The lesion involves the back of the torso. An image taken at an angle:
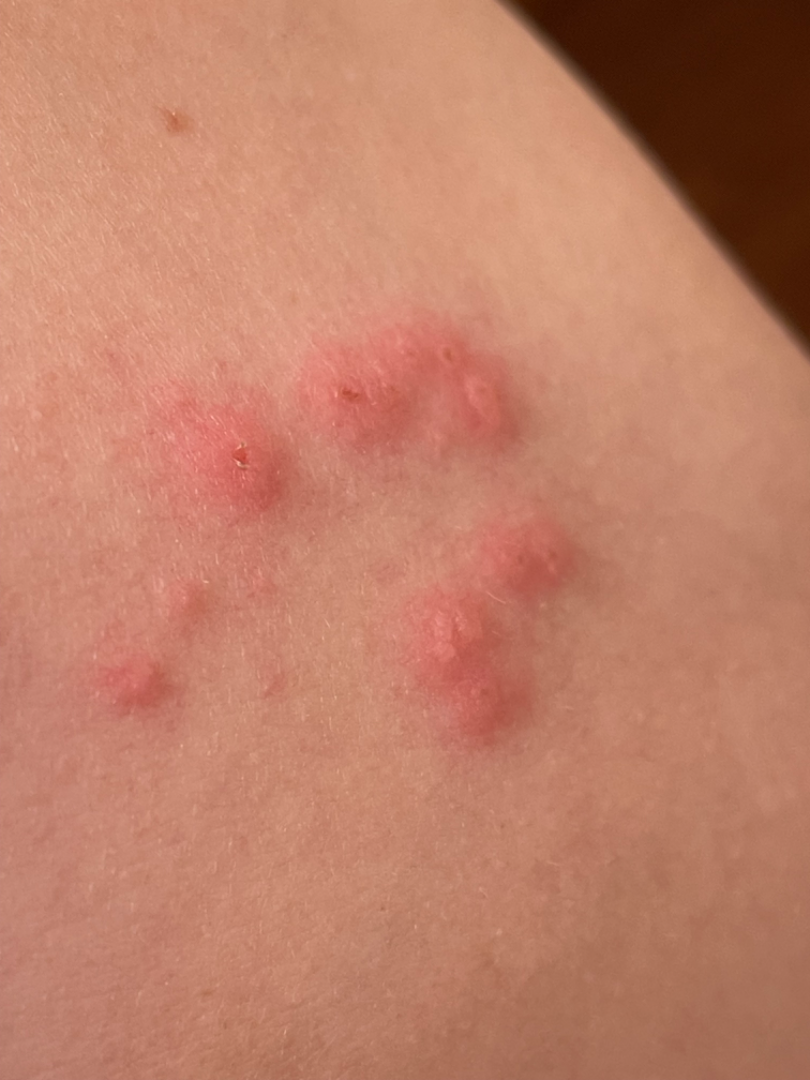| field | value |
|---|---|
| patient-reported symptoms | itching, burning and pain |
| patient describes the issue as | a rash |
| described texture | fluid-filled |
| skin tone | FST III; human graders estimated MST 2–3 |
| differential | consistent with Herpes Zoster |